Dermoscopy of a skin lesion: 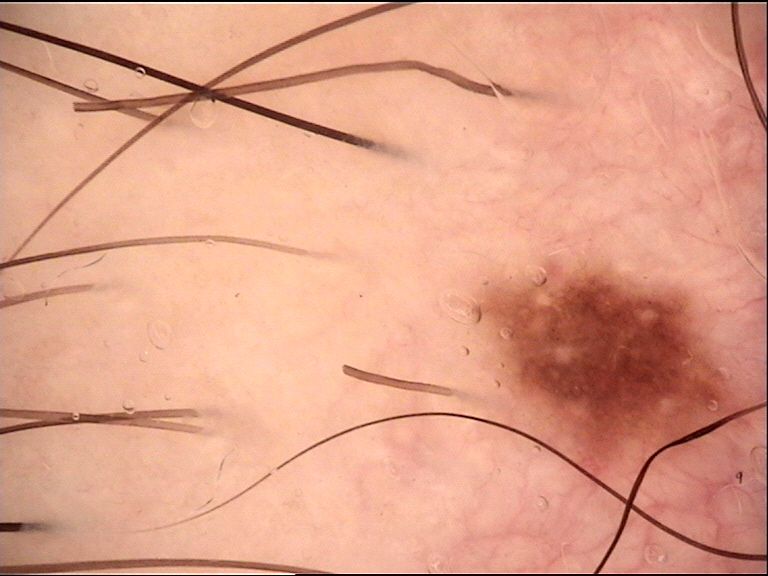Findings:
* diagnostic label — dysplastic junctional nevus (expert consensus)